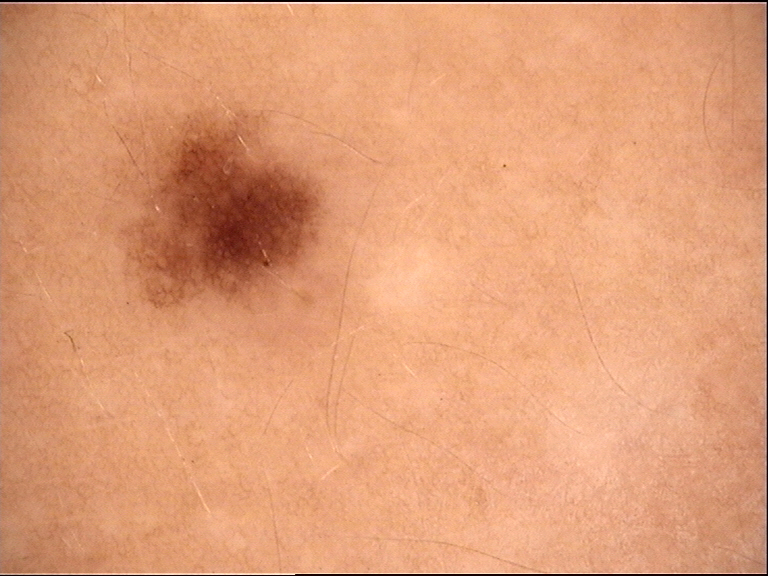The diagnosis was a benign lesion — a dysplastic junctional nevus.